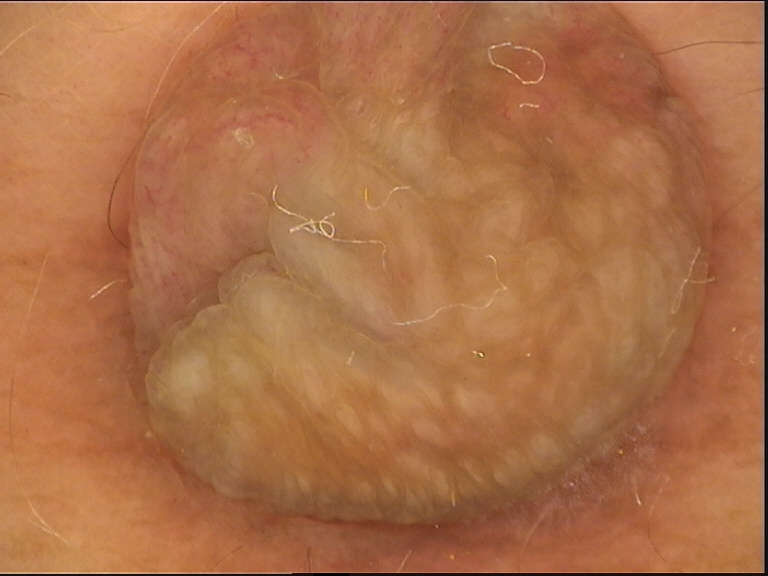A dermoscopic image of a skin lesion.
The morphology is that of a banal lesion.
Labeled as a dermal nevus.